The contributor is male · the affected area is the back of the torso · the contributor notes the lesion is raised or bumpy · reported duration is less than one week · the lesion is associated with itching · this image was taken at an angle · the patient considered this a rash — 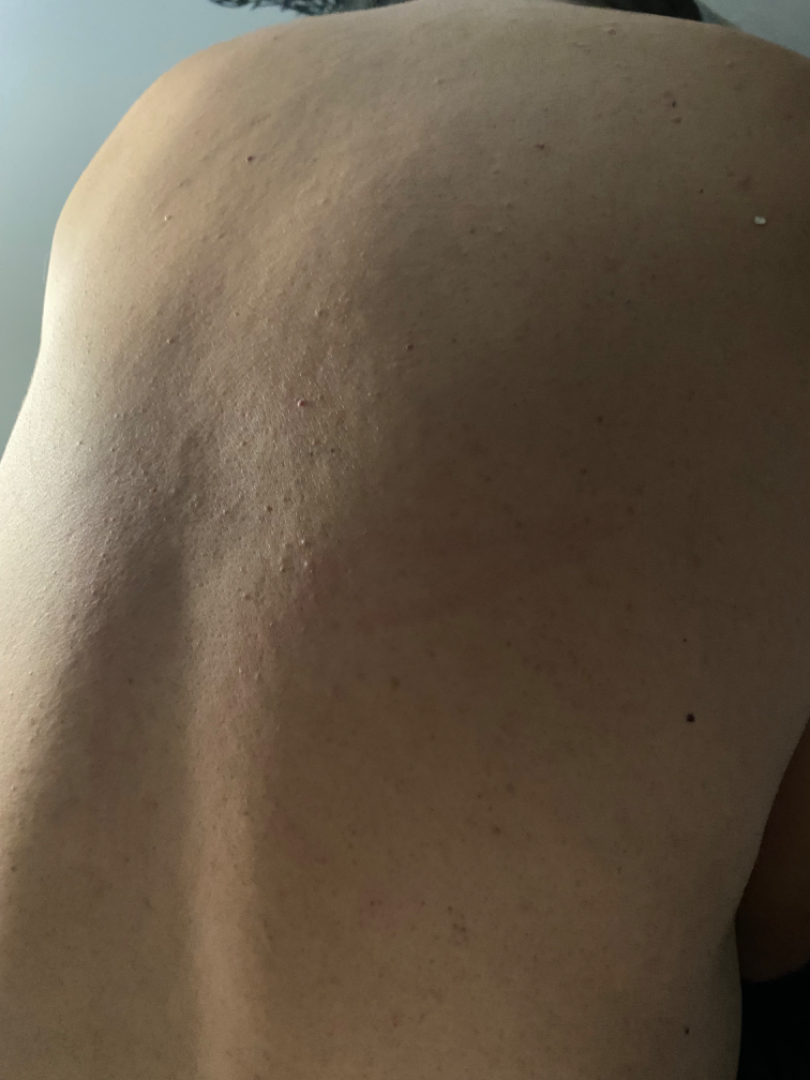{"differential": {"Drug Rash": 0.33, "Eczema": 0.33, "Hypersensitivity": 0.33}}